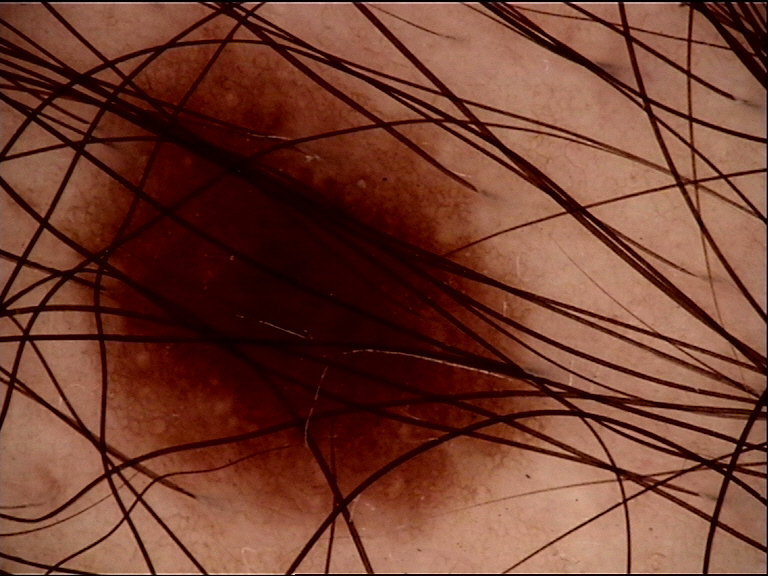Conclusion:
The diagnostic label was a dysplastic junctional nevus.